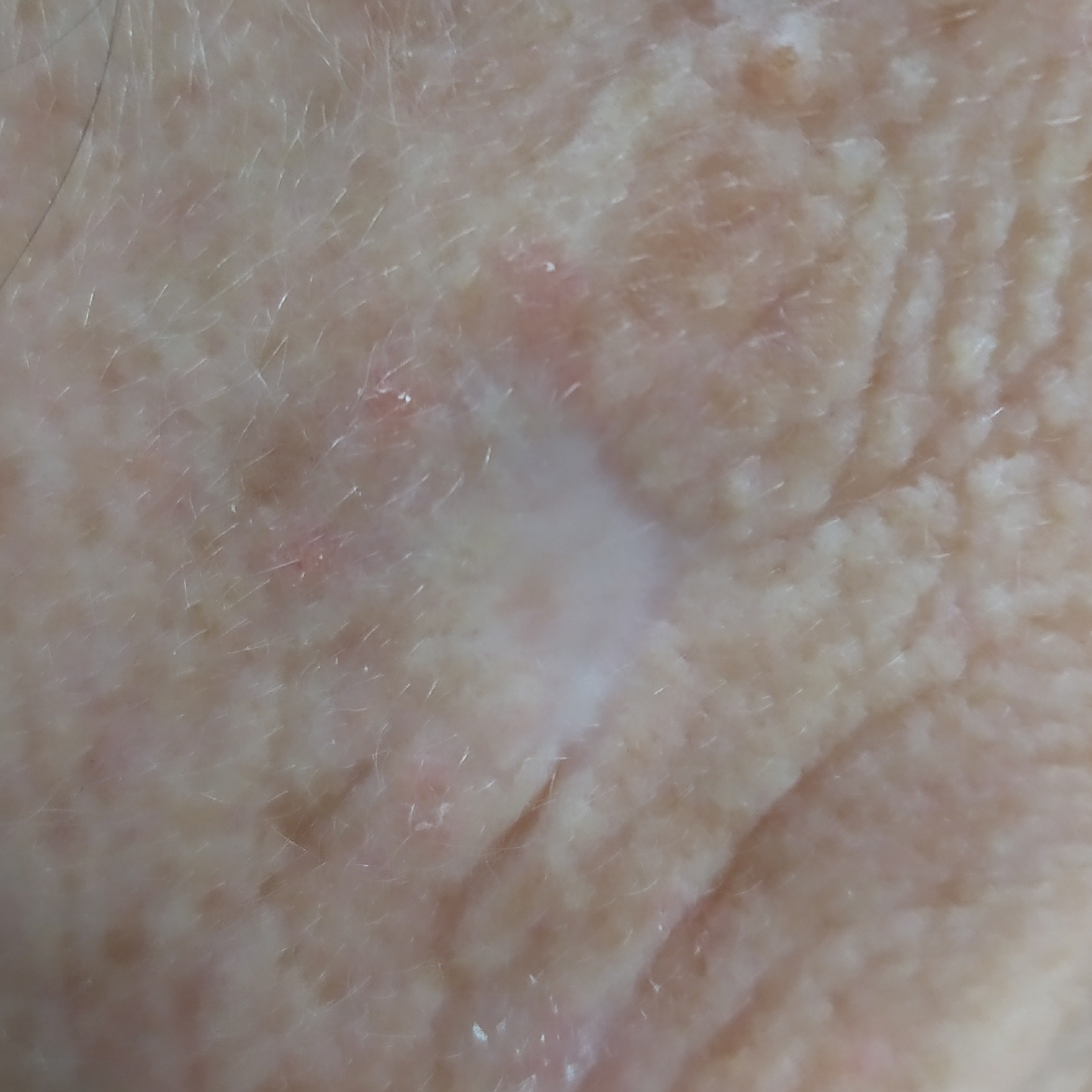A female subject 56 years of age. The lesion was found on the face. Confirmed on histopathology as an actinic keratosis.